A dermoscopic close-up of a skin lesion.
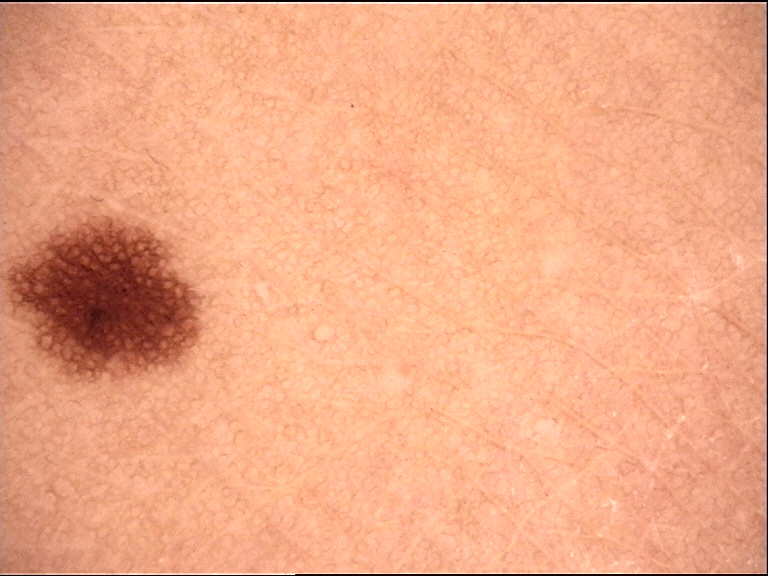Q: What is the diagnosis?
A: junctional nevus (expert consensus)